A male patient roughly 75 years of age. A skin lesion imaged with contact-polarized dermoscopy. Fitzpatrick skin type II — 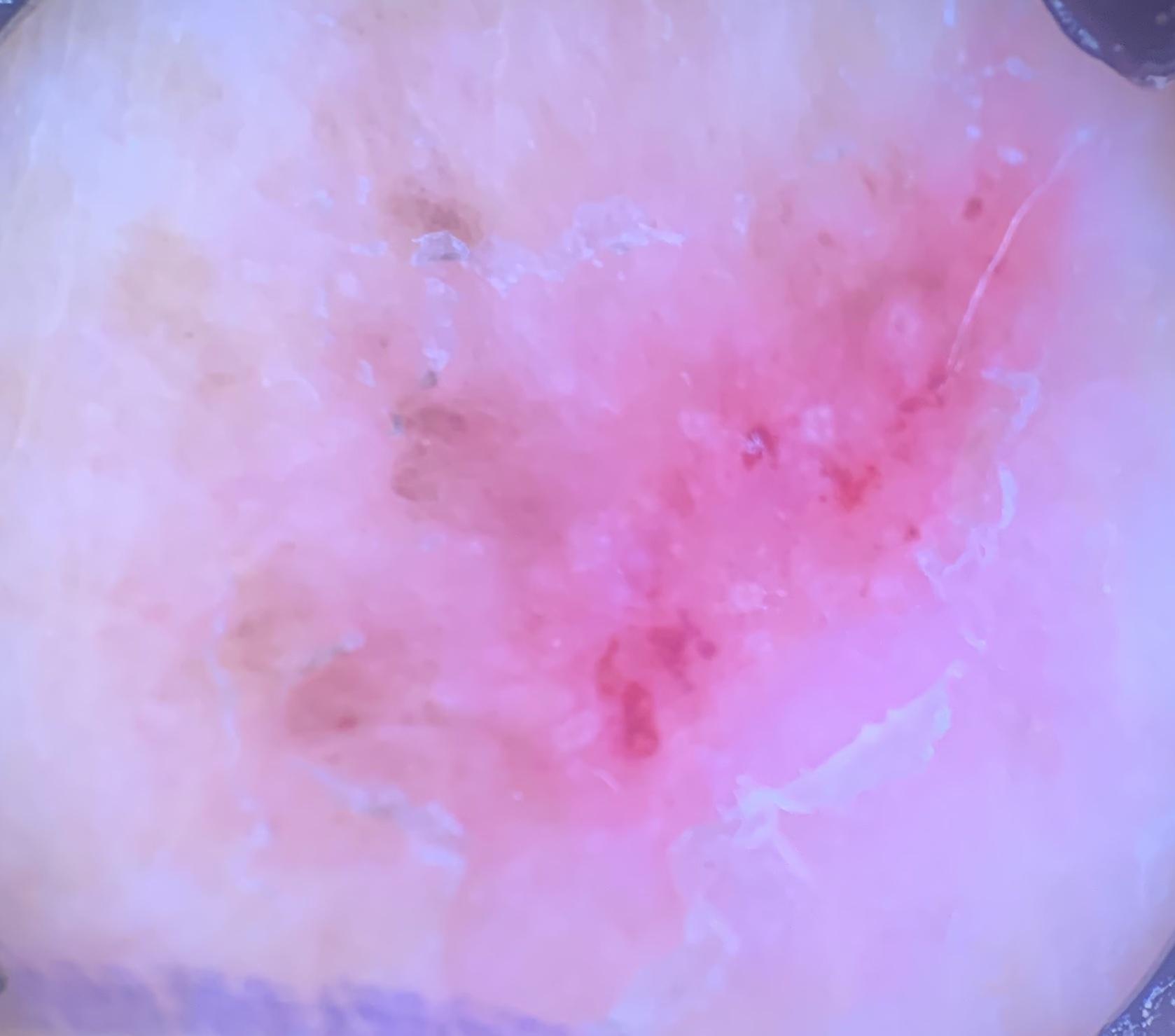body site = the trunk (the posterior trunk), pathology = Solar or actinic keratosis (biopsy-proven).